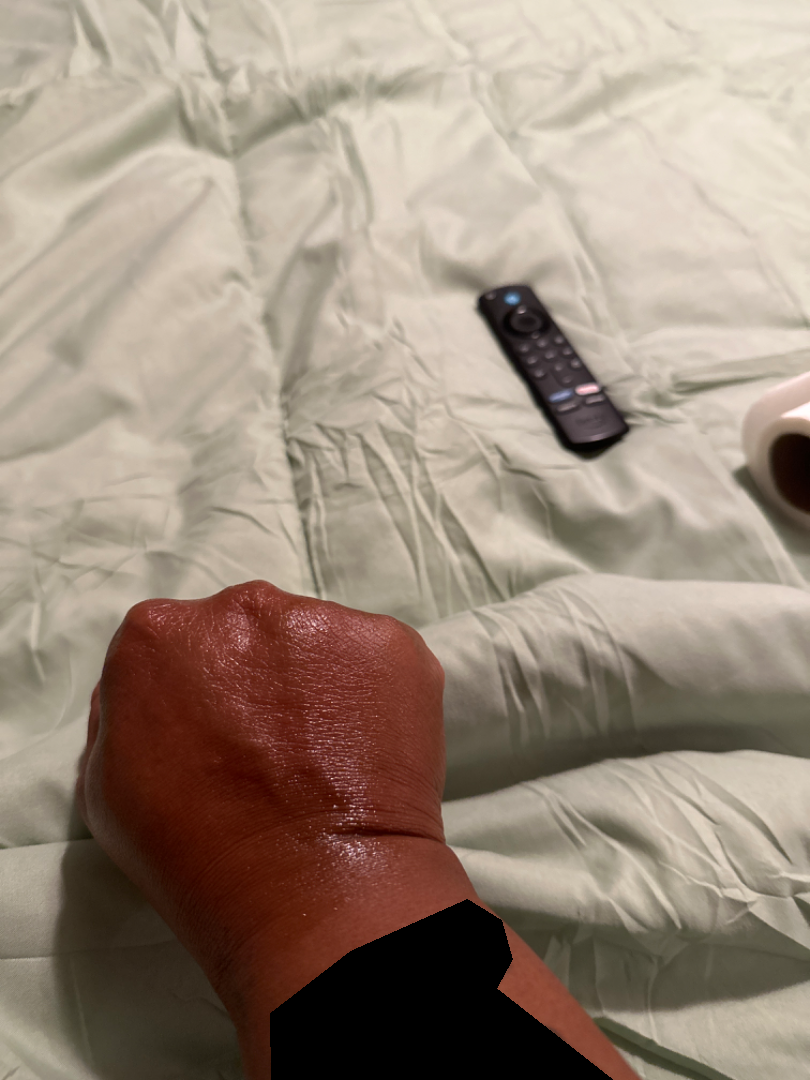{"differential": {"leading": ["Urticaria"]}}